Dermoscopy of a skin lesion:
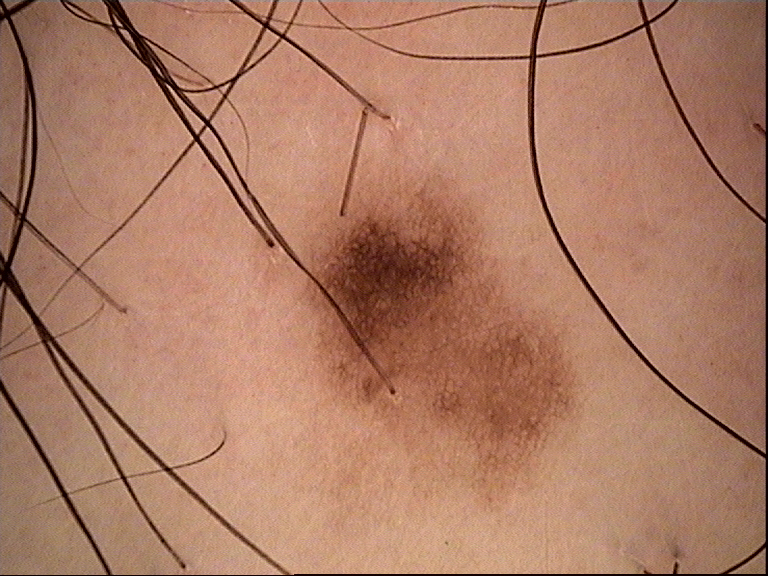The diagnostic label was a benign lesion — a dysplastic junctional nevus.